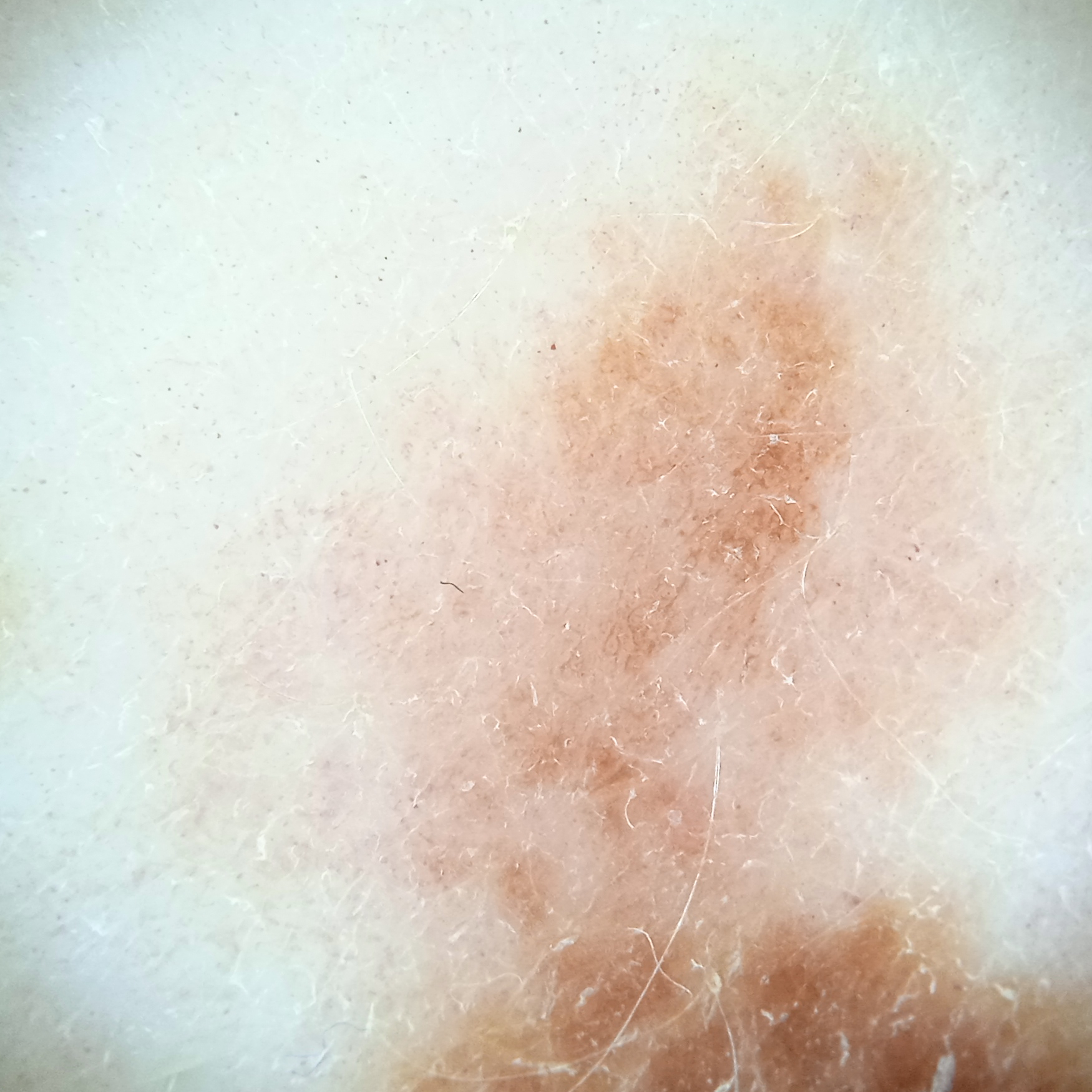A female subject age 54. The patient reports a personal history of cancer, a personal history of skin cancer, a family history of skin cancer, and no immunosuppression. The patient describes having numerous moles. The patient says their skin reddens with sun exposure. Dermoscopy of a skin lesion. Dermatologist review favored a melanoma.